A female patient aged 77 · the patient was assessed as Fitzpatrick III · a clinical photograph showing a skin lesion:
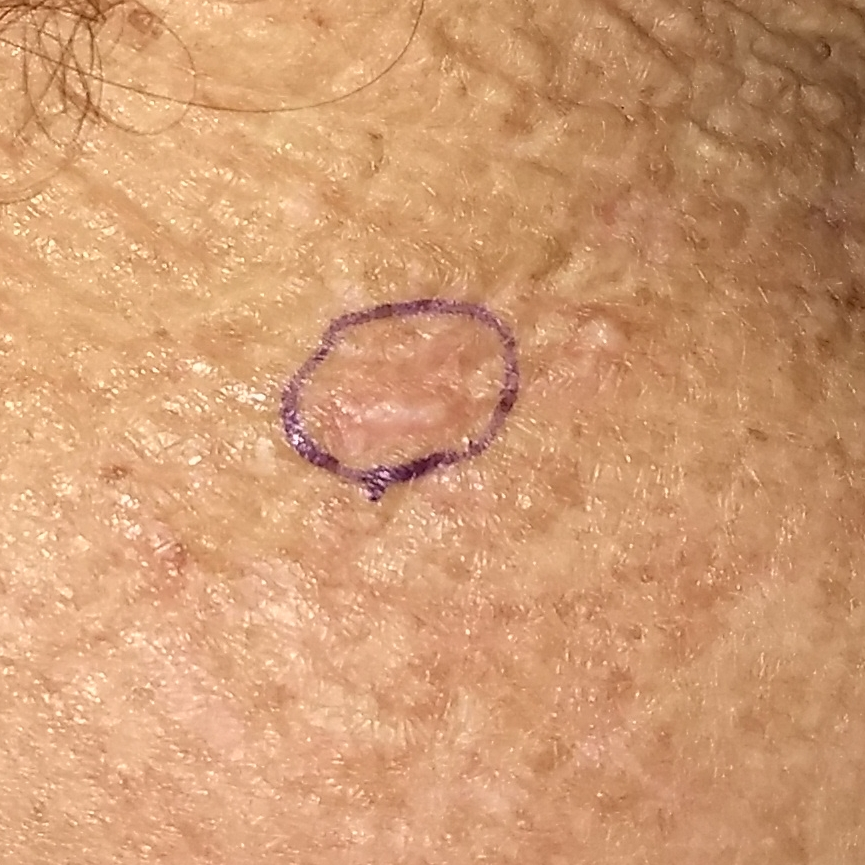Q: What is the anatomic site?
A: the neck
Q: How large is the lesion?
A: 25 × 10 mm
Q: What symptoms does the patient report?
A: itching, bleeding / no elevation, no change in appearance
Q: What did the workup show?
A: actinic keratosis (biopsy-proven)